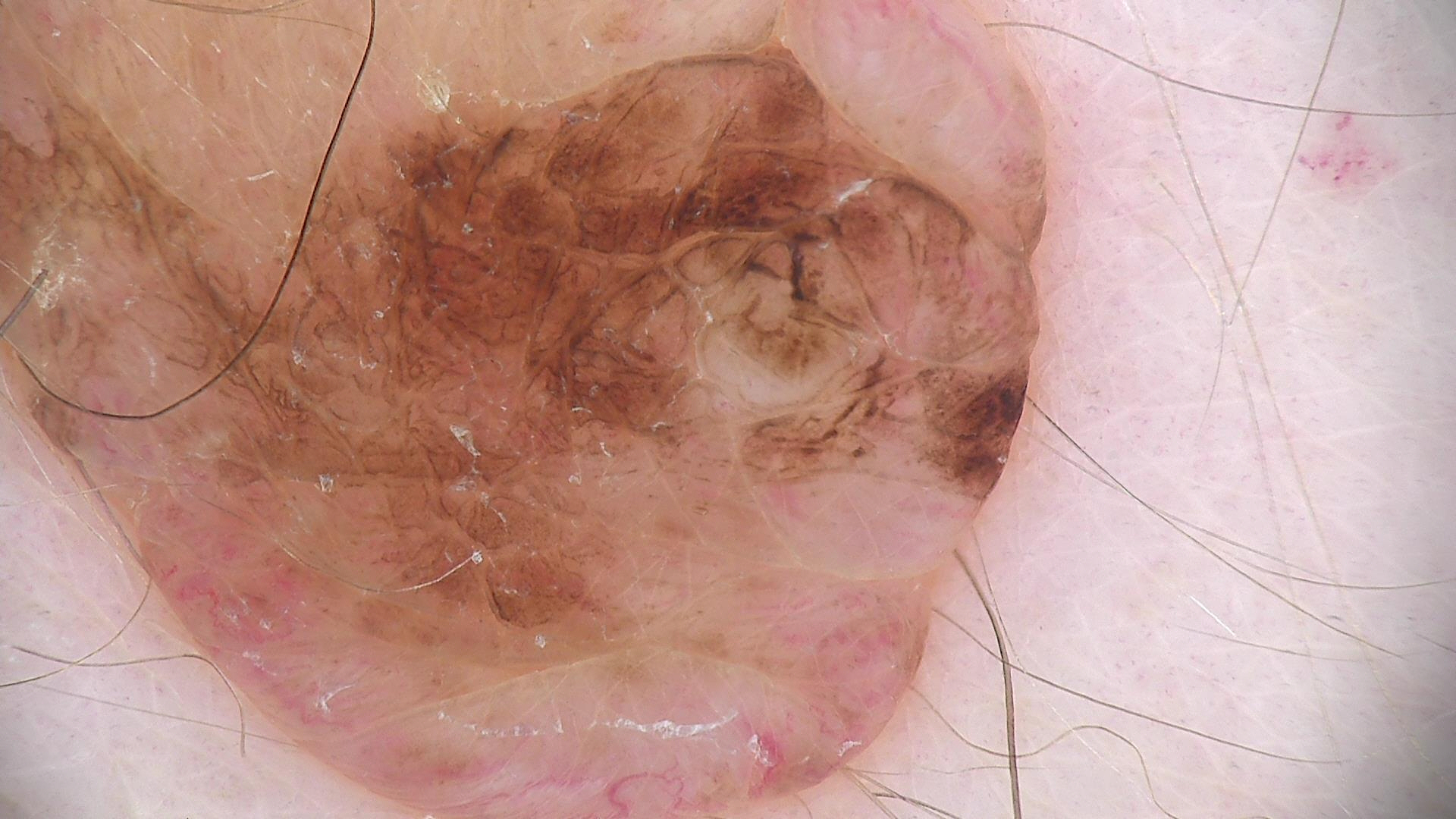Findings:
A dermoscopic close-up of a skin lesion. The architecture is that of a banal lesion.
Impression:
The diagnosis was a dermal nevus.